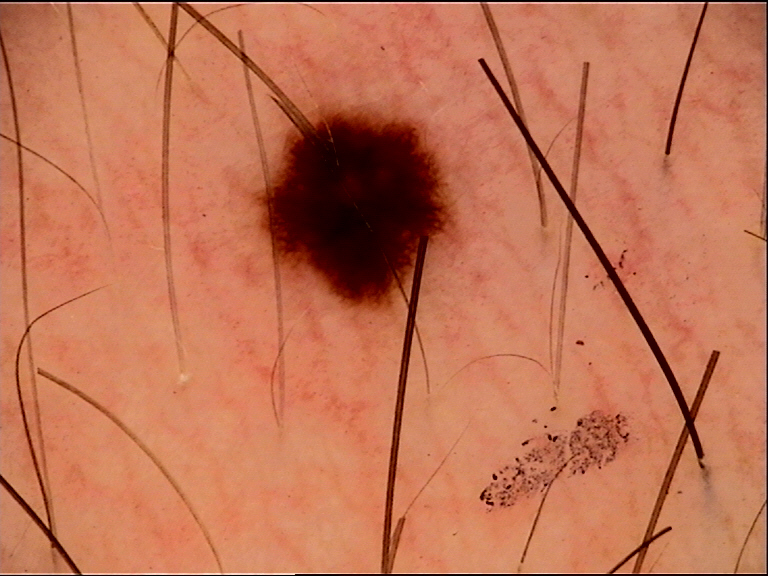image type — dermoscopy | classification — banal | class — junctional nevus (expert consensus).